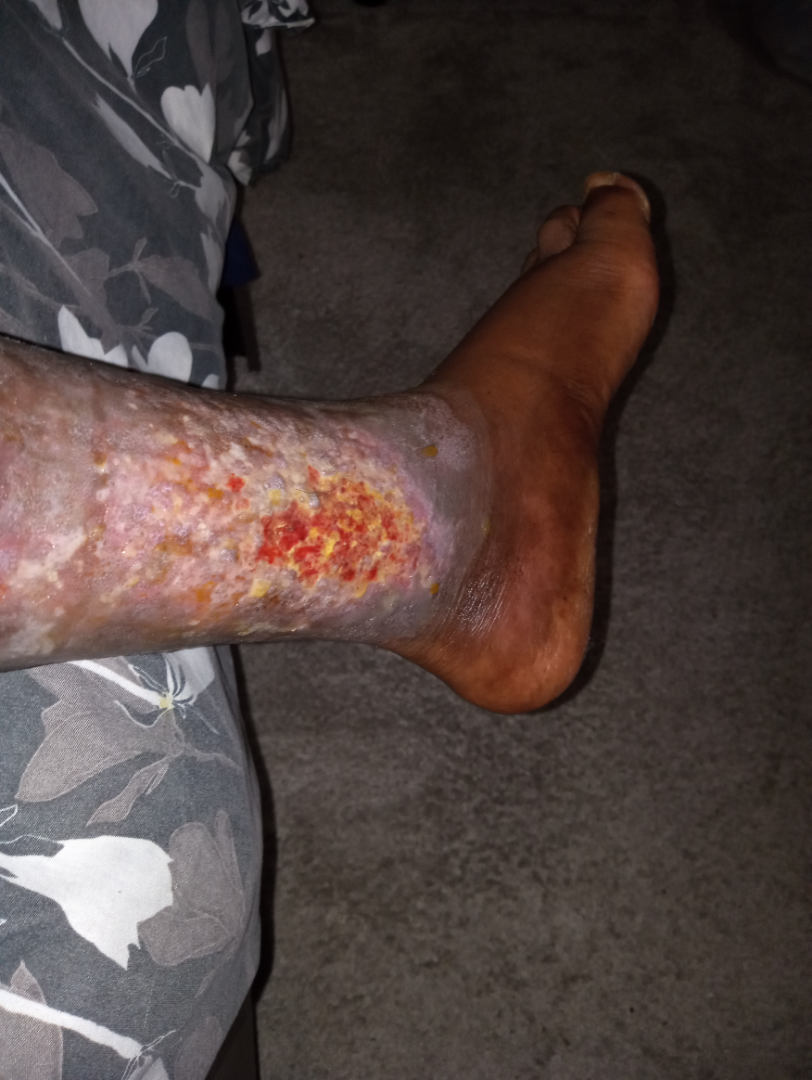| feature | finding |
|---|---|
| photo taken | close-up |
| lesion texture | fluid-filled and rough or flaky |
| contributor | female, age 50–59 |
| present for | three to twelve months |
| site | leg |
| differential | Infected eczema (weight 0.67); Stasis Dermatitis (weight 0.33) |